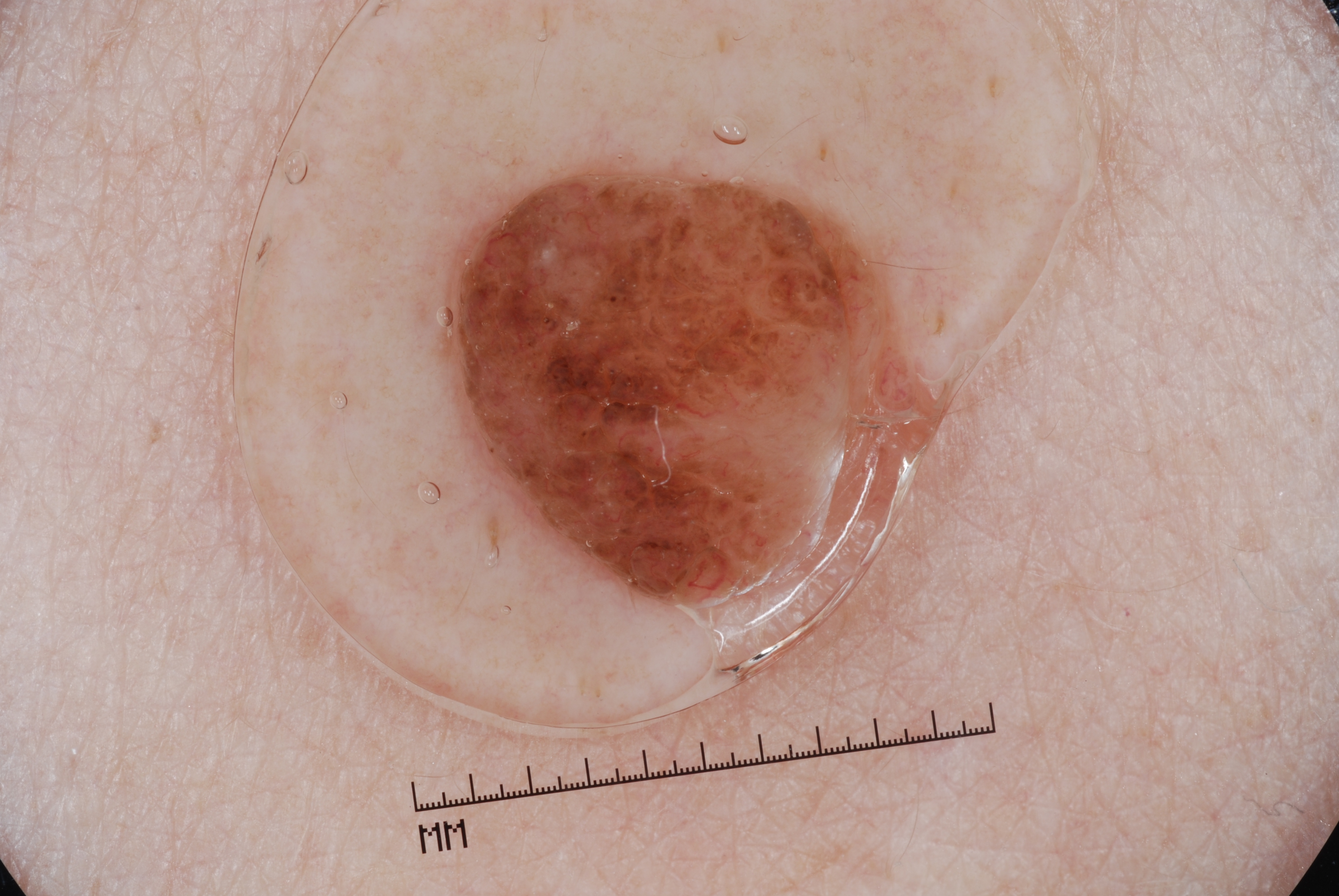| key | value |
|---|---|
| imaging | dermoscopy |
| location | 449/165/899/605 |
| lesion extent | moderate |
| dermoscopic findings | globules; absent: streaks, negative network, milia-like cysts, and pigment network |
| assessment | a melanocytic nevus |